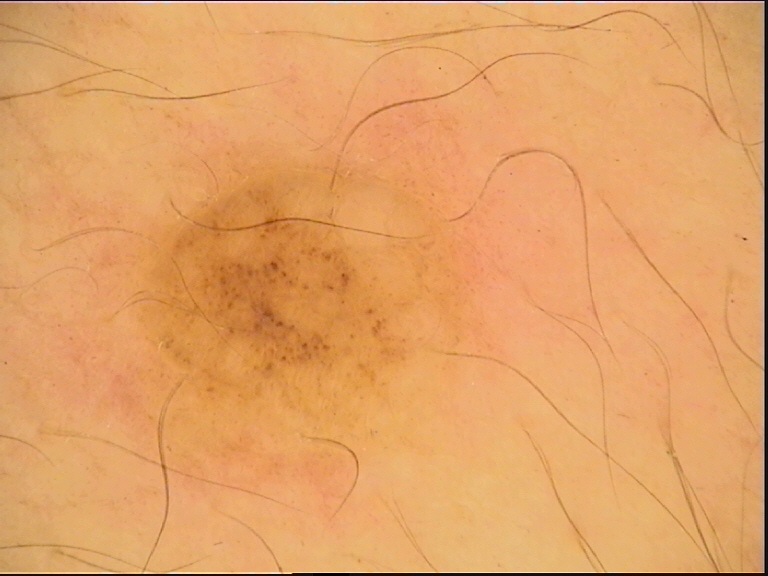A dermatoscopic image of a skin lesion. The morphology is that of a banal lesion. Classified as a dermal nevus.